Recorded as Fitzpatrick phototype III · contact-polarized dermoscopy of a skin lesion · a male subject in their 40s · the chart notes melanoma in a first-degree relative.
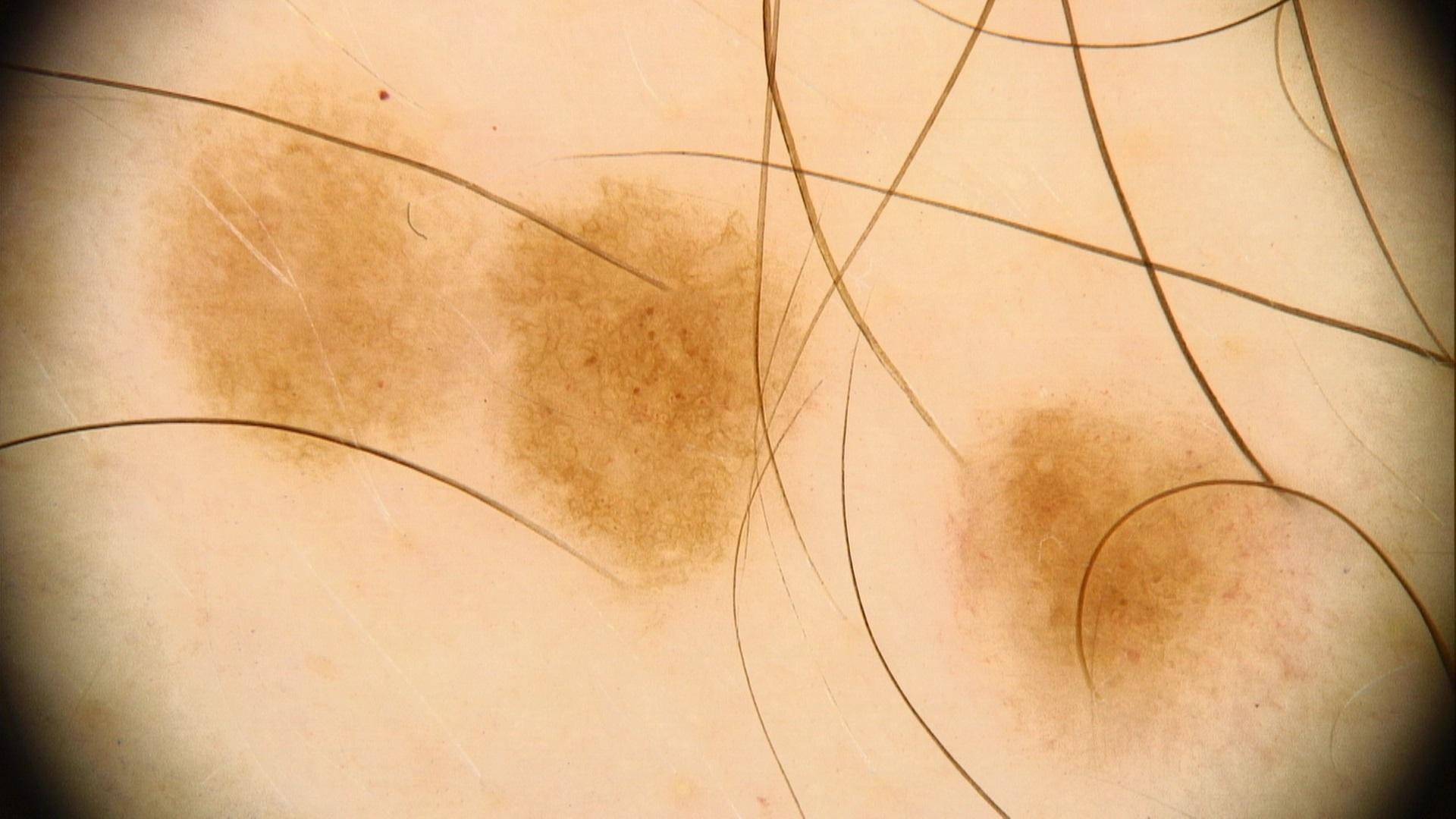The lesion is on the trunk (the anterior trunk).
Clinically diagnosed as a lesion of melanocytic lineage — a nevus.